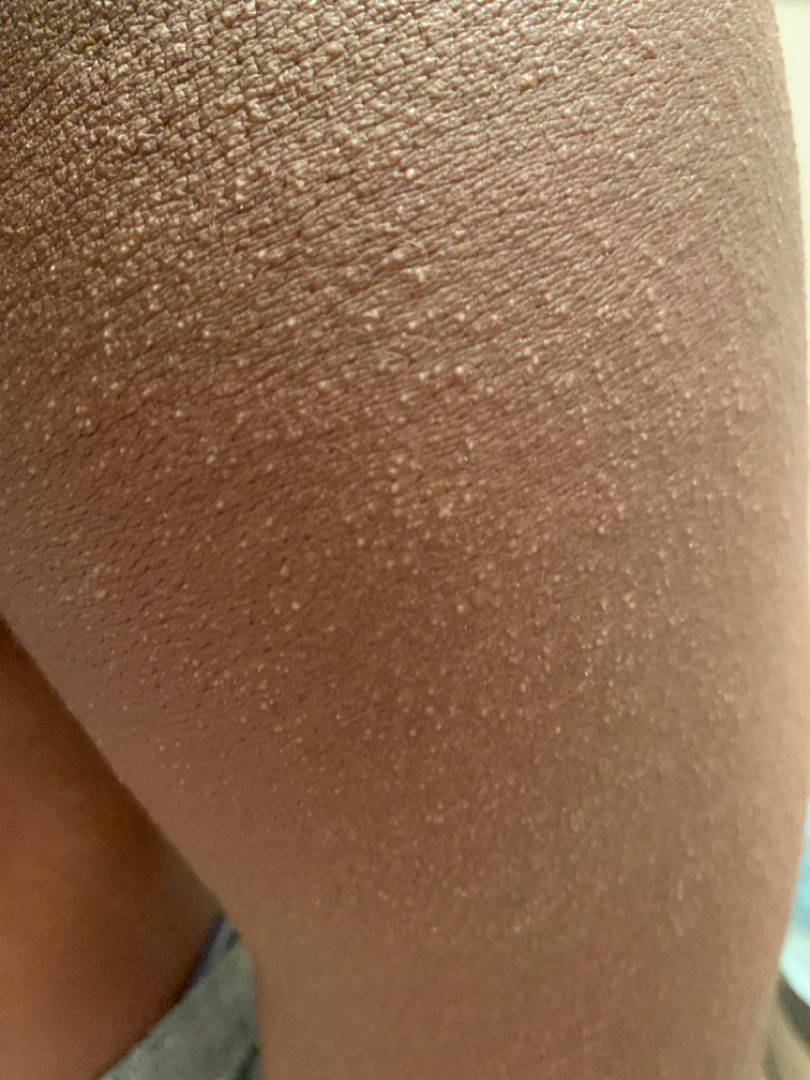<summary>
<assessment>could not be assessed</assessment>
<body_site>back of the torso, back of the hand</body_site>
<texture>fluid-filled, rough or flaky</texture>
<shot_type>at an angle</shot_type>
</summary>